A subject about 55 years old; the patient is Fitzpatrick phototype II; a clinical overview photograph of a skin lesion:
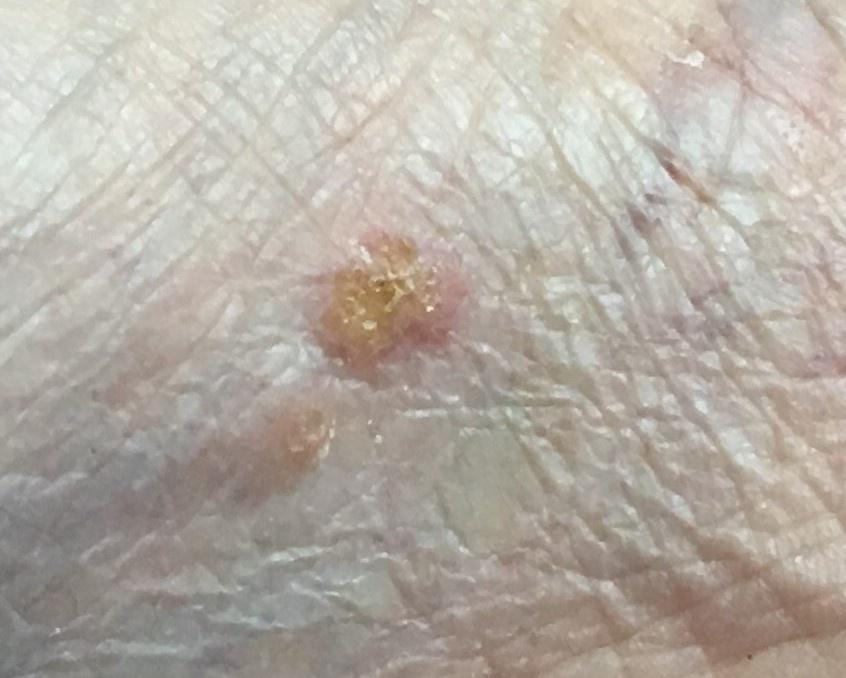site — an acral site (palms or soles); diagnostic label — Basal cell carcinoma (biopsy-proven).